Fitzpatrick III. The chart records prior skin cancer (patient or family):
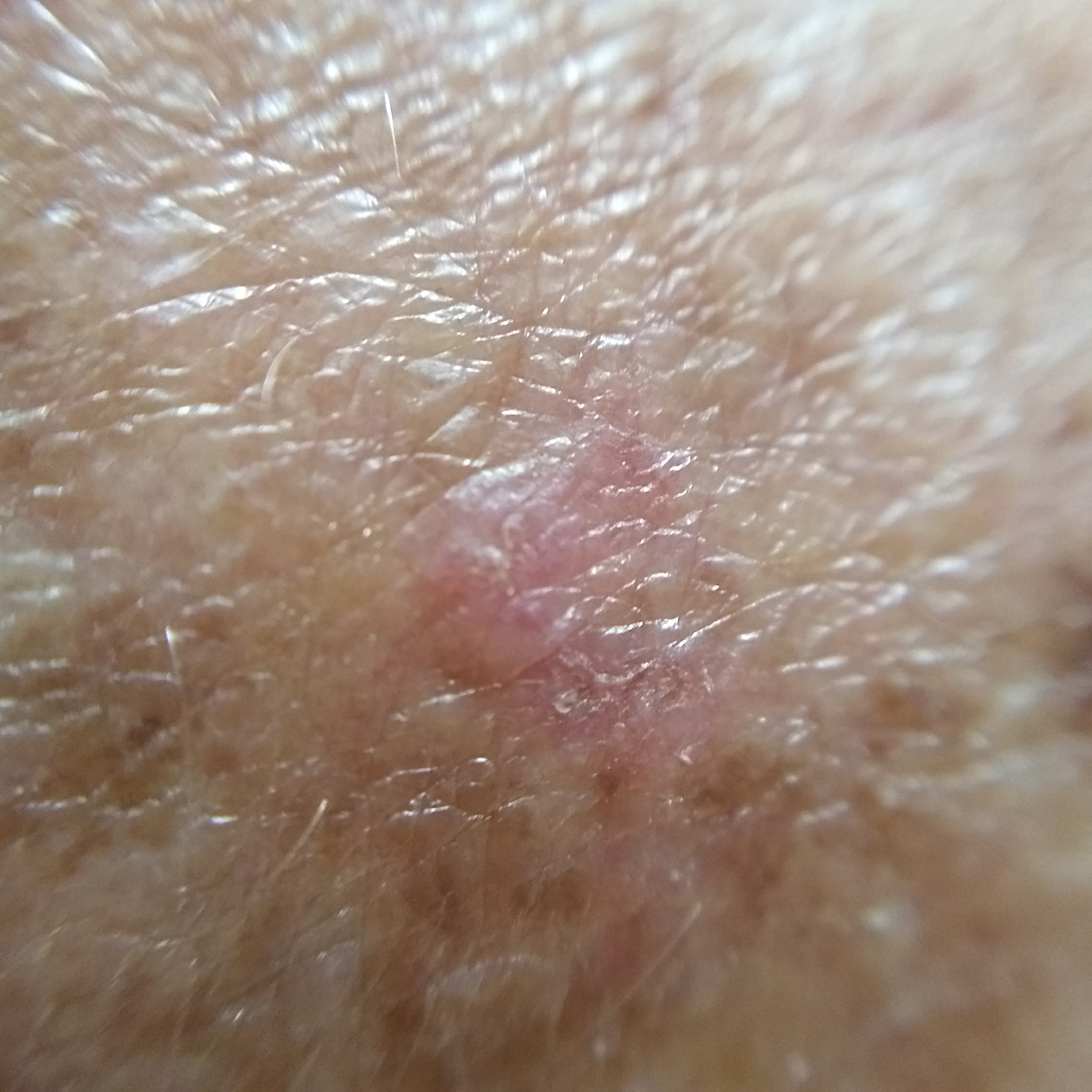region=a hand; lesion size=2 × 2 mm; patient-reported symptoms=itching / no bleeding, no elevation; diagnostic label=actinic keratosis (clinical consensus).